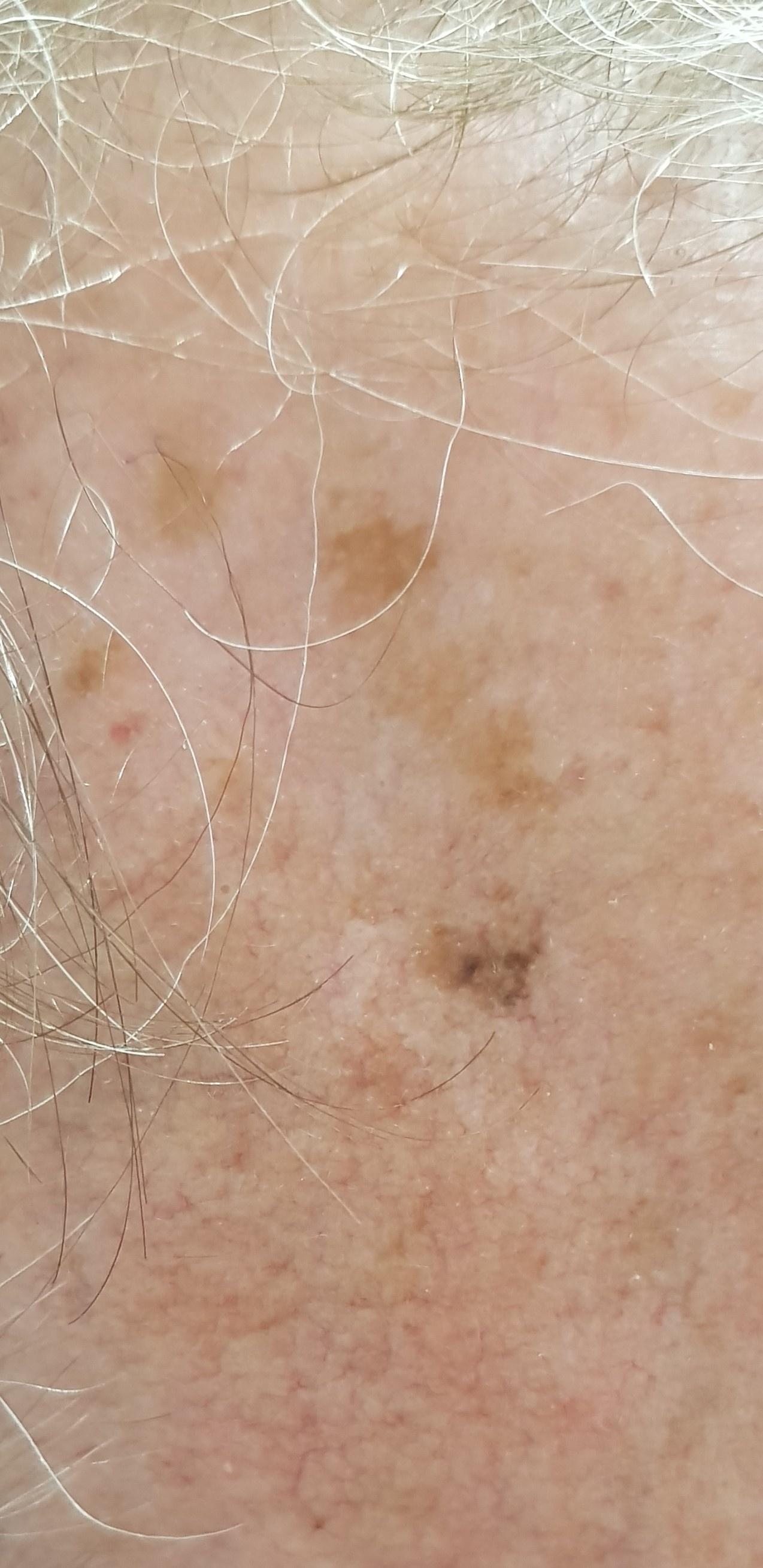Q: What is the diagnosis?
A: Melanoma (biopsy-proven)